The contributor is 50–59, male; an image taken at a distance; the affected area is the leg: 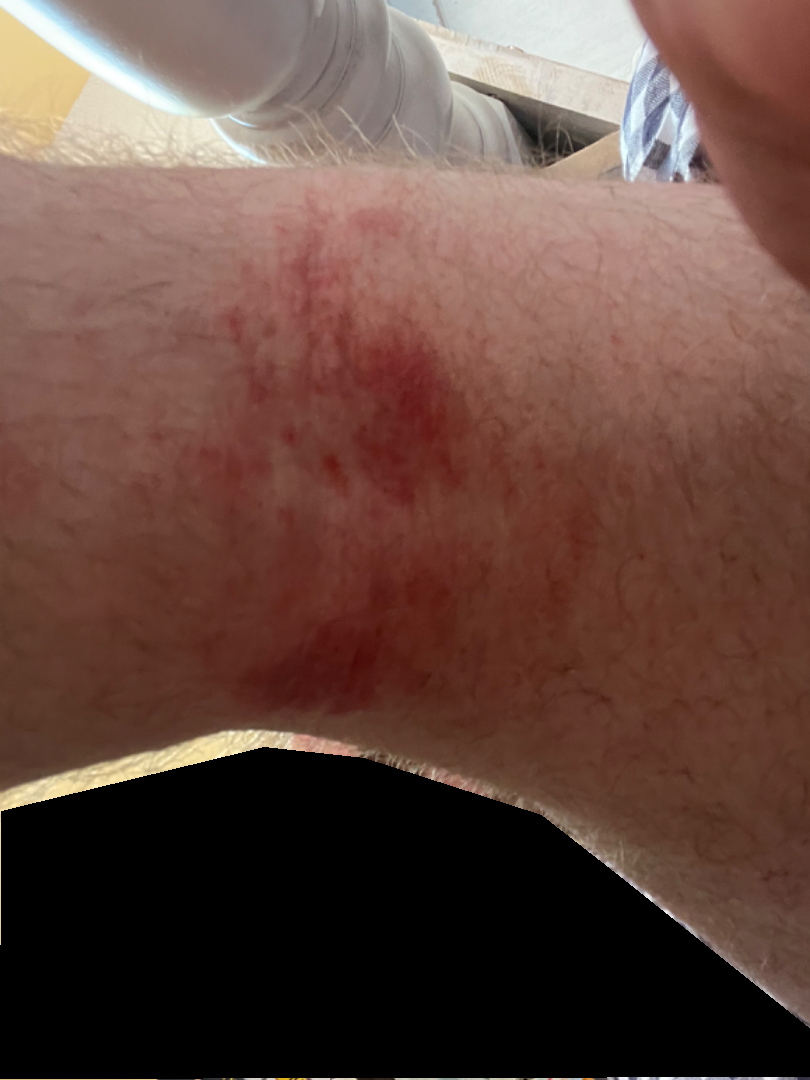<dermatology_case>
<differential>
  <Eczema>0.33</Eczema>
  <Allergic Contact Dermatitis>0.23</Allergic Contact Dermatitis>
  <Irritant Contact Dermatitis>0.21</Irritant Contact Dermatitis>
  <Abrasion, scrape, or scab>0.13</Abrasion, scrape, or scab>
  <Acute dermatitis, NOS>0.1</Acute dermatitis, NOS>
</differential>
</dermatology_case>